A dermoscopic close-up of a skin lesion: 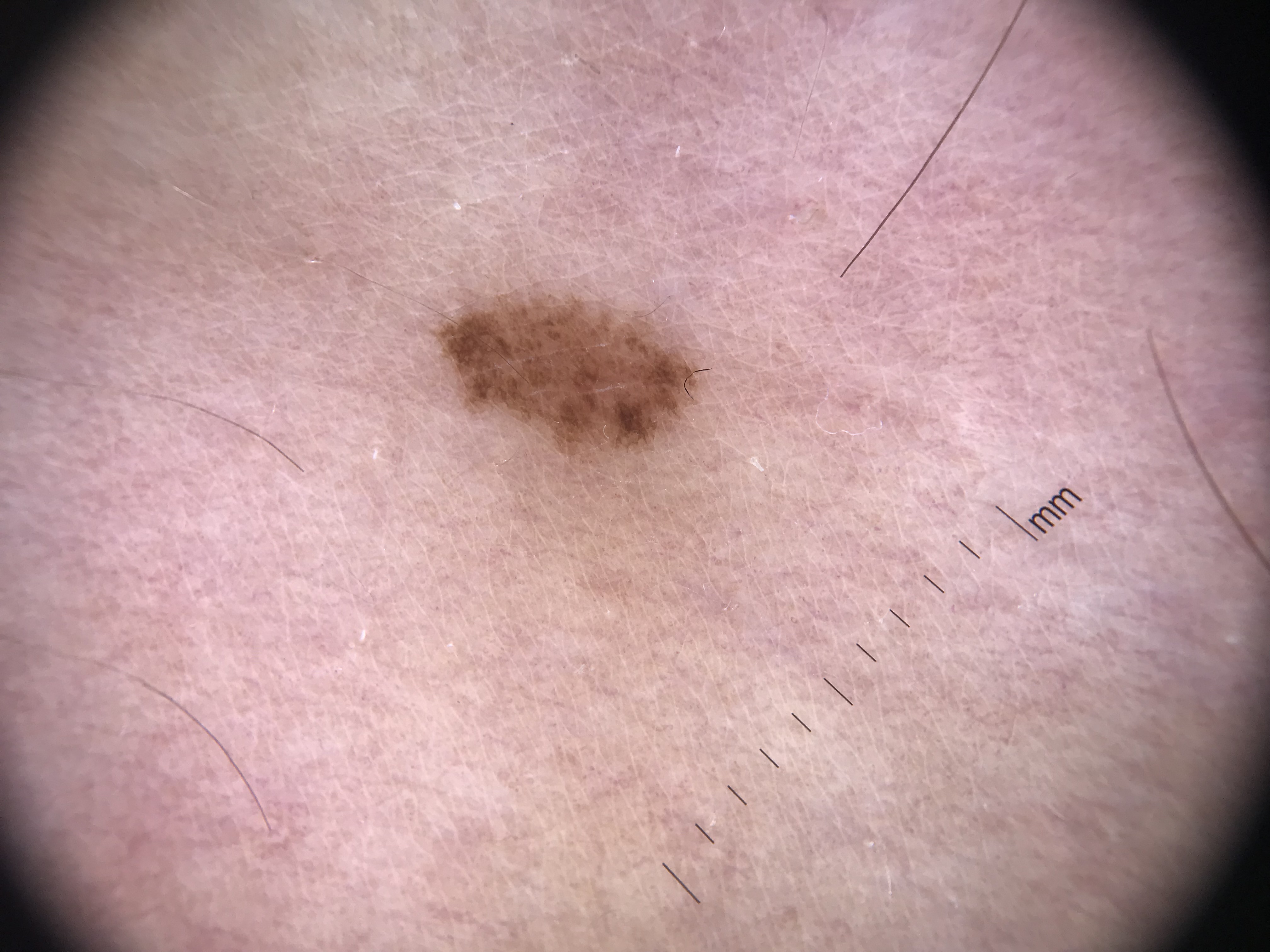Conclusion:
Diagnosed as a dysplastic junctional nevus.